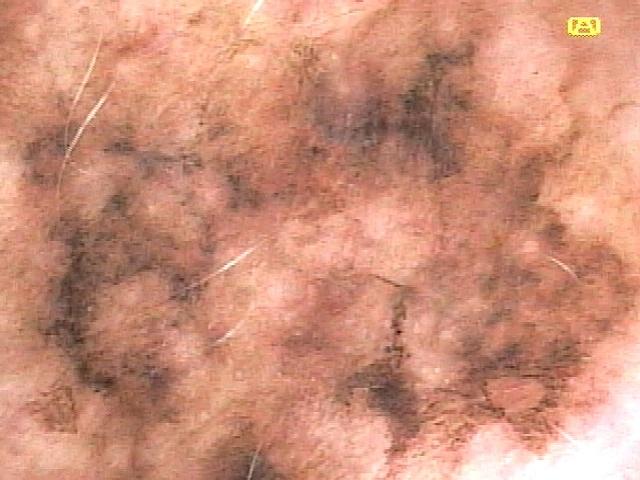| feature | finding |
|---|---|
| melanoma history | a prior melanoma but no first-degree relative with melanoma |
| patient | female, aged around 70 |
| skin type | I |
| image type | dermoscopy |
| site | the trunk |
| pathology | Melanoma (biopsy-proven) |